Skin tone: Fitzpatrick phototype I · an image taken at an angle · the patient is a male aged 18–29:
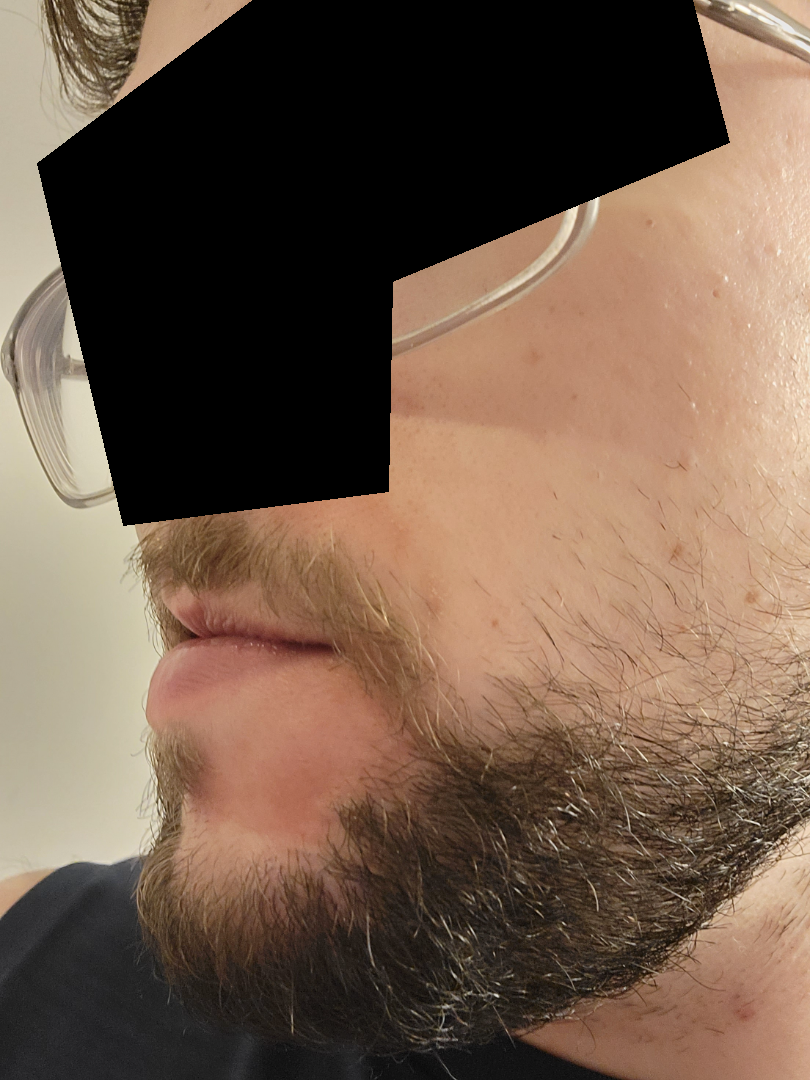diagnostic considerations — the reviewer's impression was Seborrheic Dermatitis.